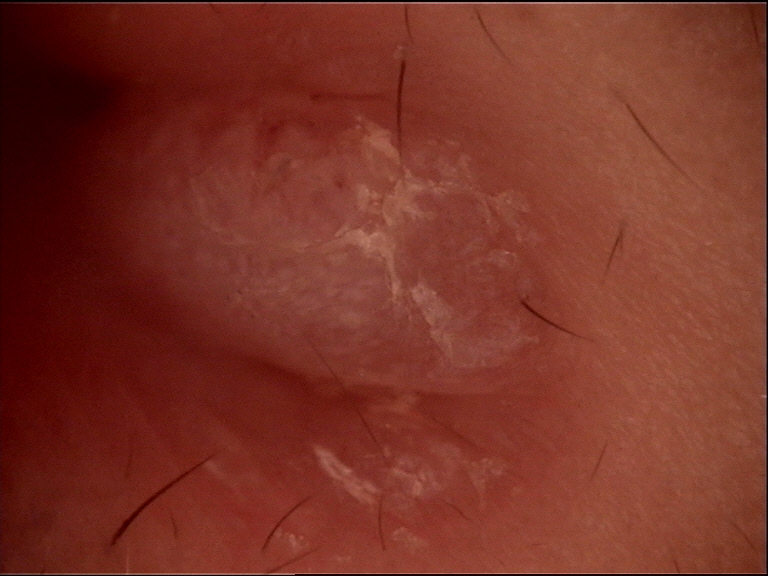<dermoscopy>
  <image>dermatoscopy</image>
  <lesion_type>
    <main_class>keratinocytic</main_class>
  </lesion_type>
  <diagnosis>
    <name>squamous cell carcinoma</name>
    <code>scc</code>
    <malignancy>malignant</malignancy>
    <super_class>non-melanocytic</super_class>
    <confirmation>histopathology</confirmation>
  </diagnosis>
</dermoscopy>